Close-up view.
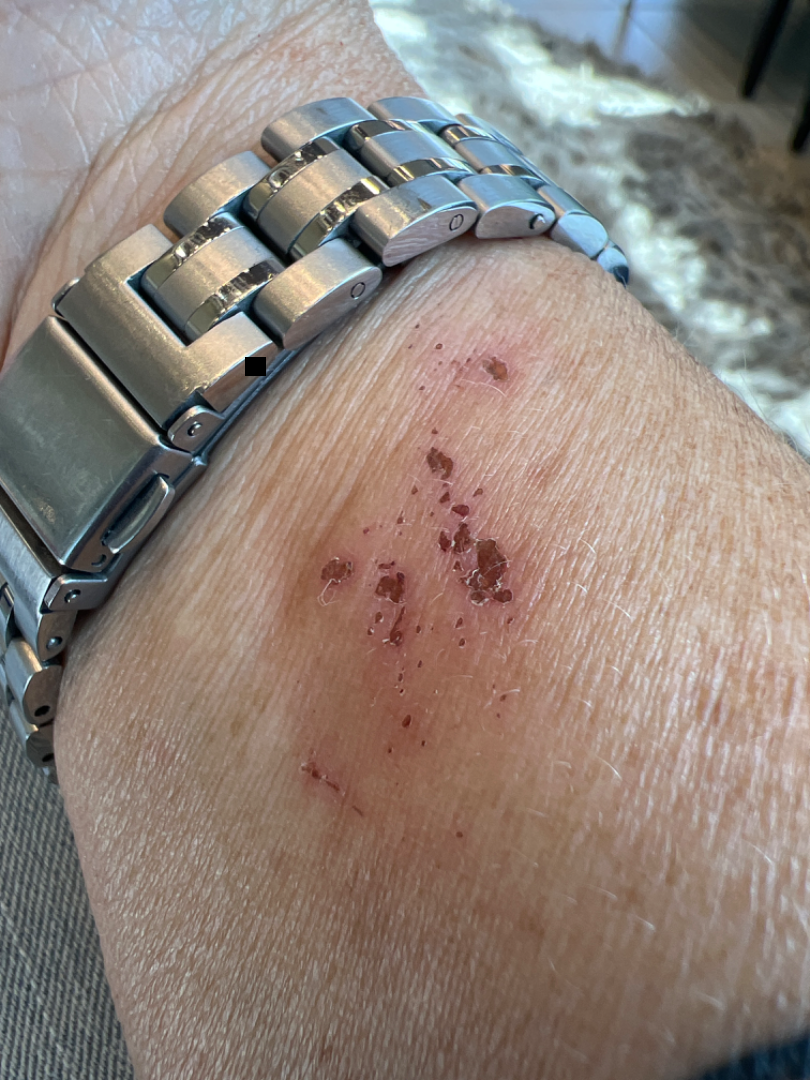differential diagnosis = Irritant Contact Dermatitis (favored).